A close-up photograph; the contributor is a male aged 18–29; the affected area is the arm: 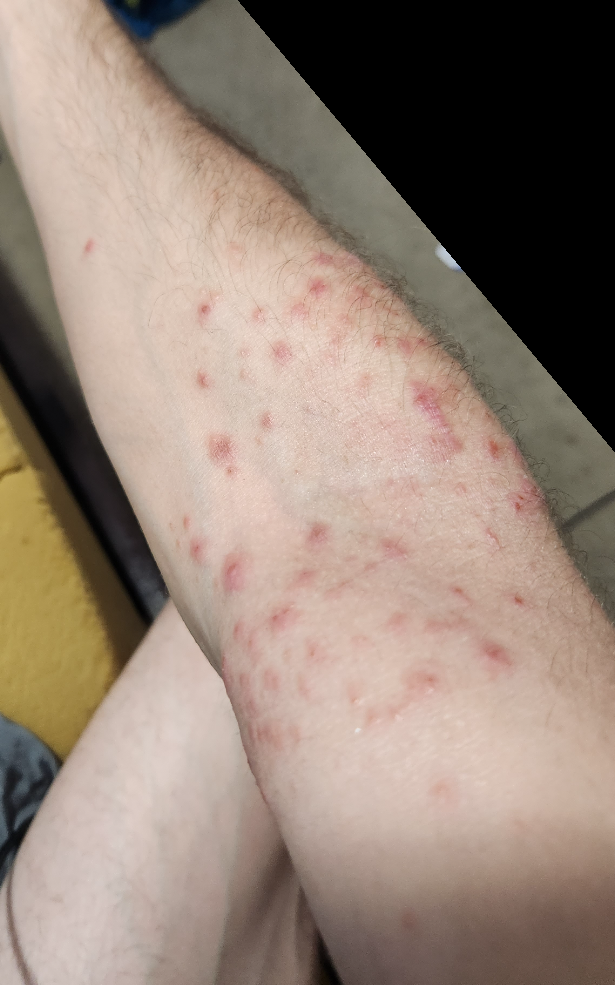Background:
The patient considered this a rash. The contributor notes the condition has been present for one to four weeks. Skin tone: Fitzpatrick II; lay graders estimated Monk skin tone scale 2–3.
Findings:
The reviewing clinician's impression was: most likely Viral Exanthem; possibly Scabies; less probable is Eczema.